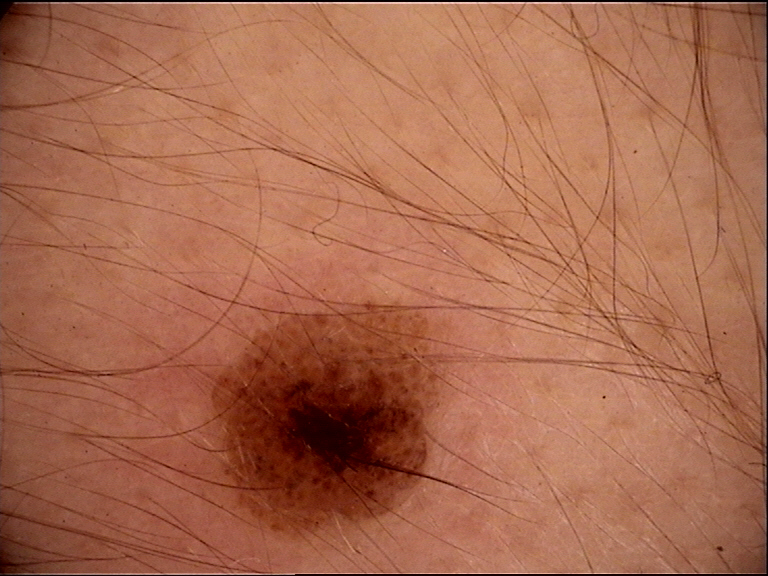classification: banal
diagnosis: compound nevus (expert consensus)